A dermoscopic image of a skin lesion:
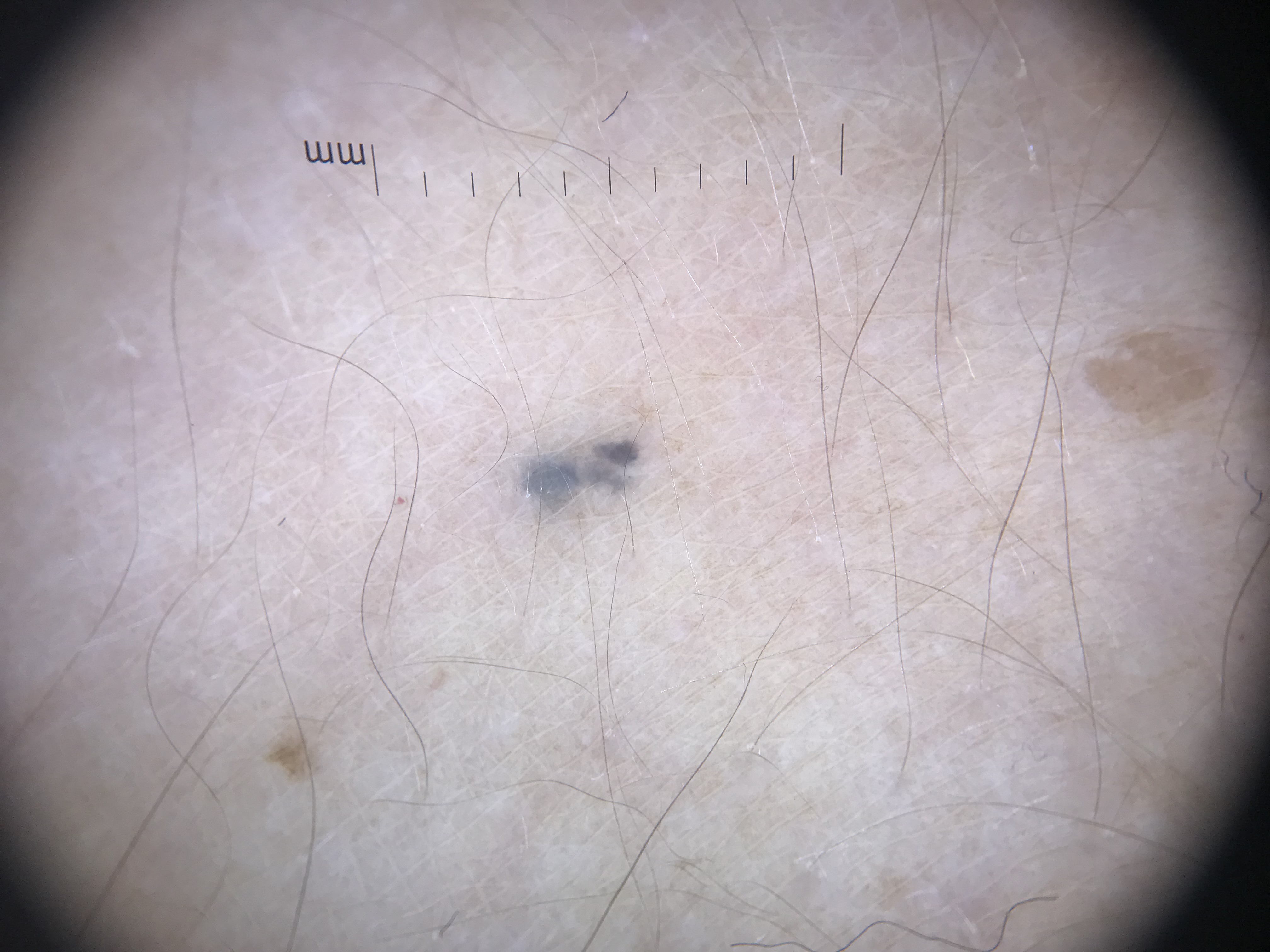Impression: Diagnosed as a banal lesion — a blue nevus.